This image was taken at an angle.
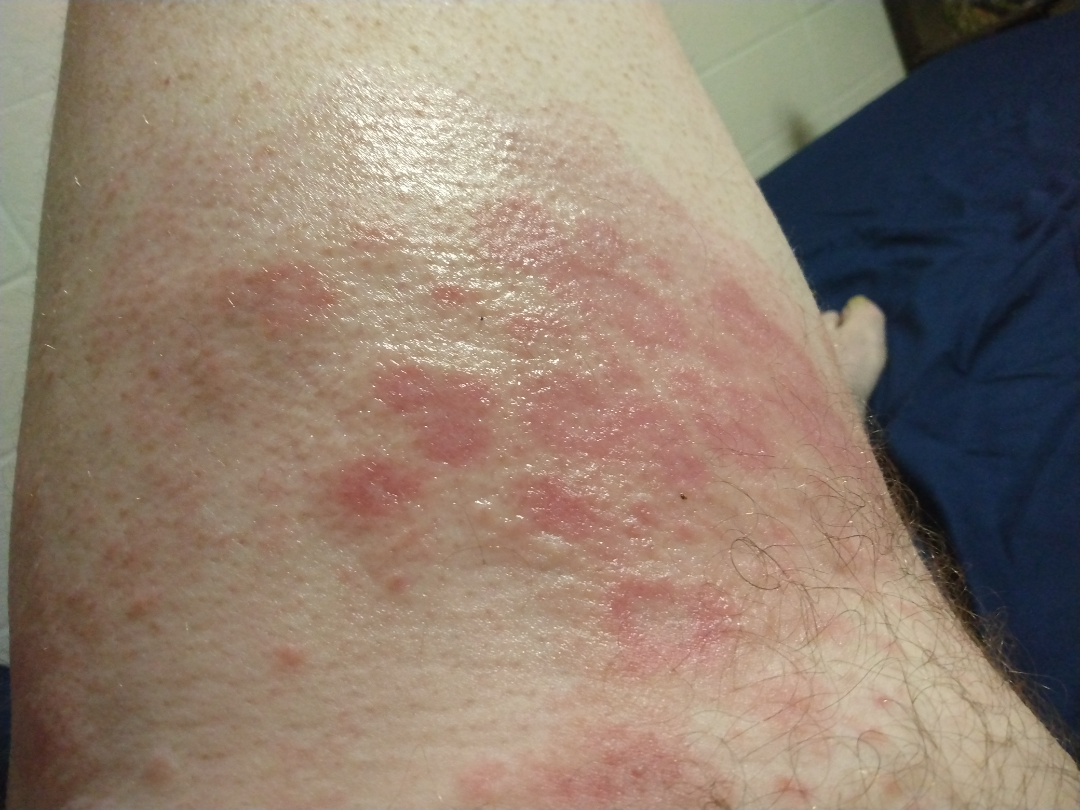<case>
  <differential>
    <leading>Urticaria</leading>
    <considered>Erythema multiforme, Allergic Contact Dermatitis</considered>
  </differential>
</case>